Dermoscopy of a skin lesion. A female subject about 35 years old:
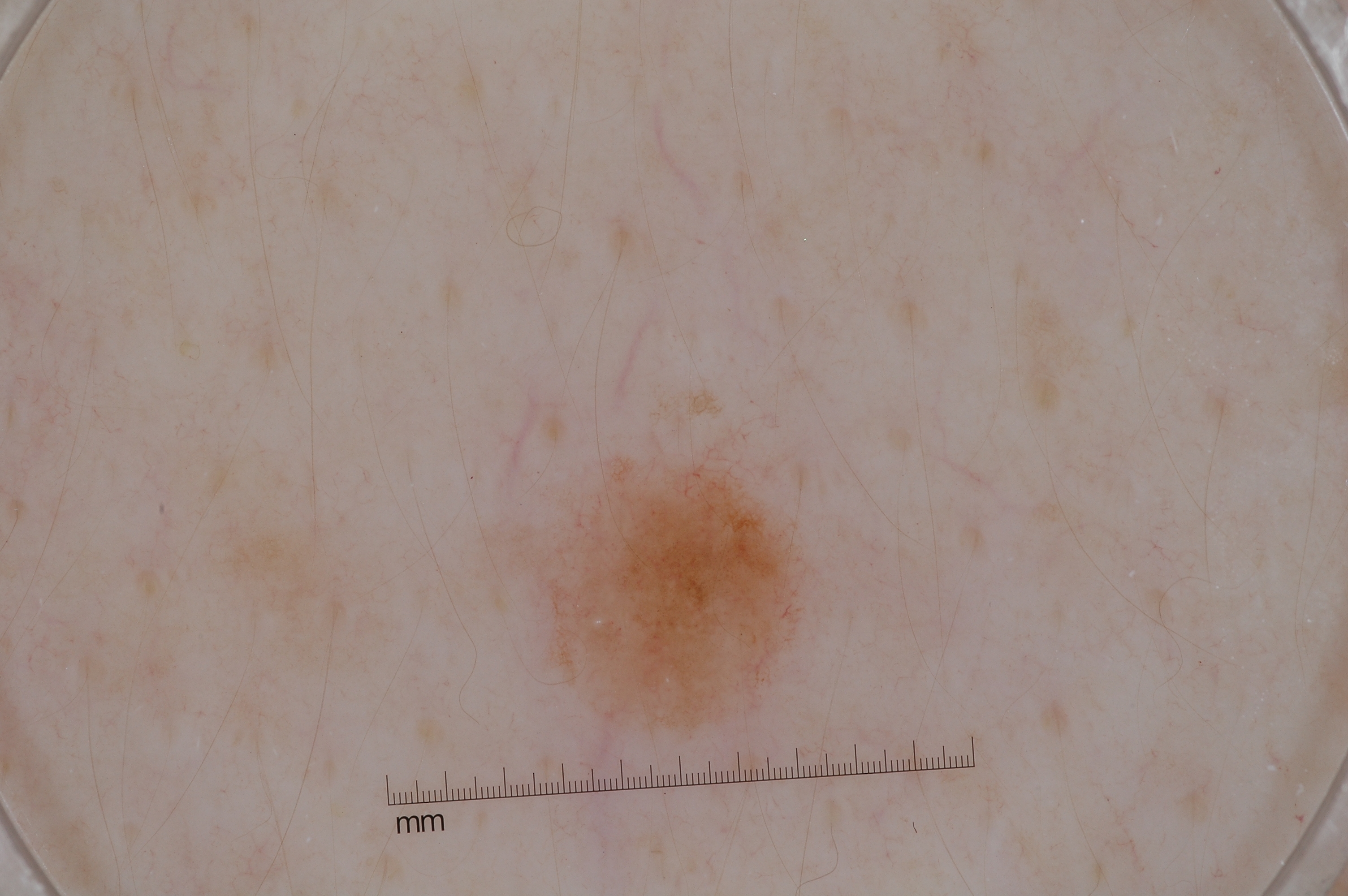lesion bbox — 530/446/811/739 | extent — small | dermoscopic features — pigment network; absent: negative network, milia-like cysts, and streaks | diagnostic label — a melanocytic nevus, a benign skin lesion.